A female subject about 50 years old · contact-polarized dermoscopy of a skin lesion · FST II — 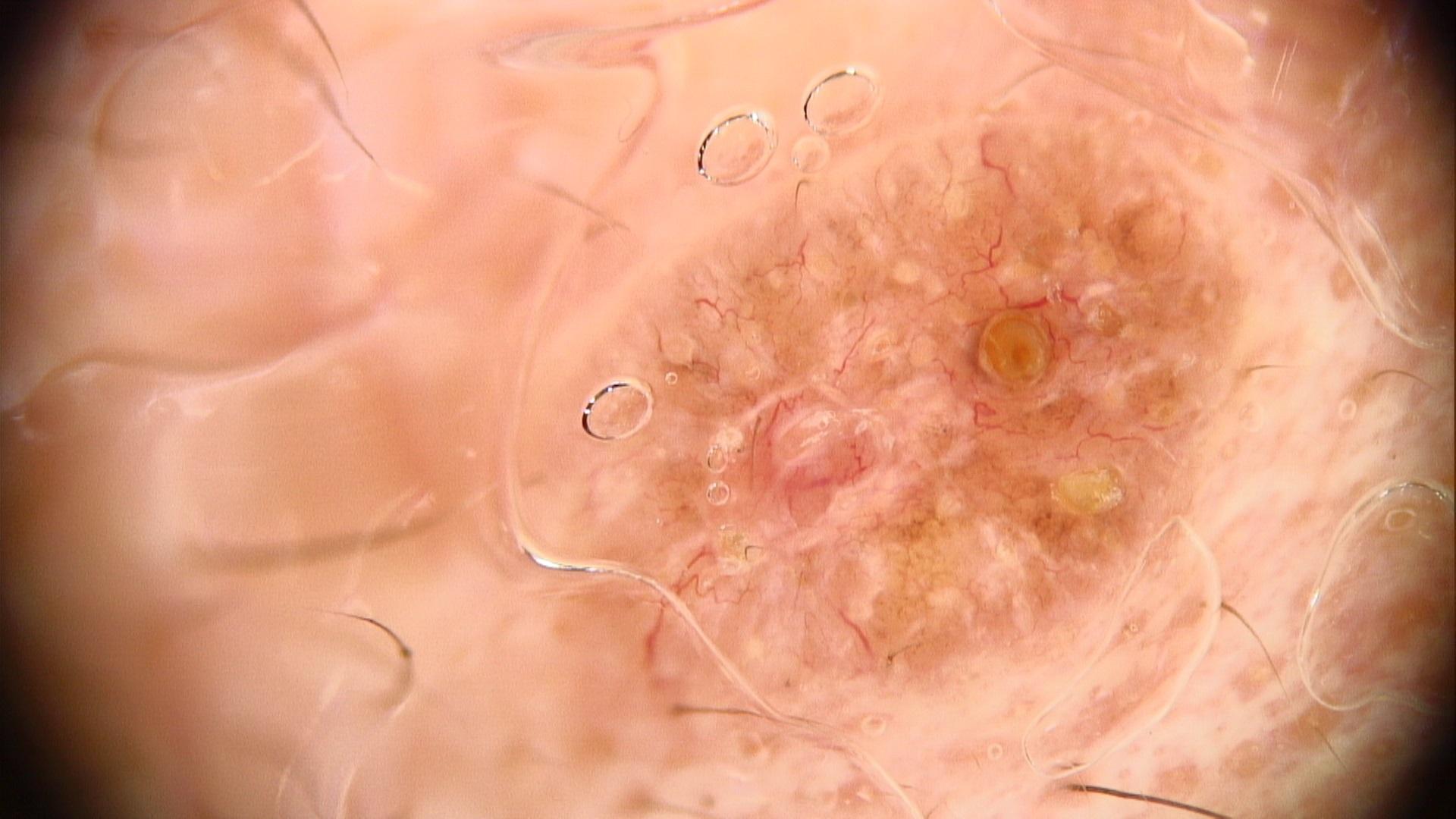{"lesion_location": {"region": "the trunk", "detail": "the posterior trunk"}, "diagnosis": {"name": "Basal cell carcinoma", "malignancy": "malignant", "confirmation": "histopathology", "lineage": "adnexal"}}